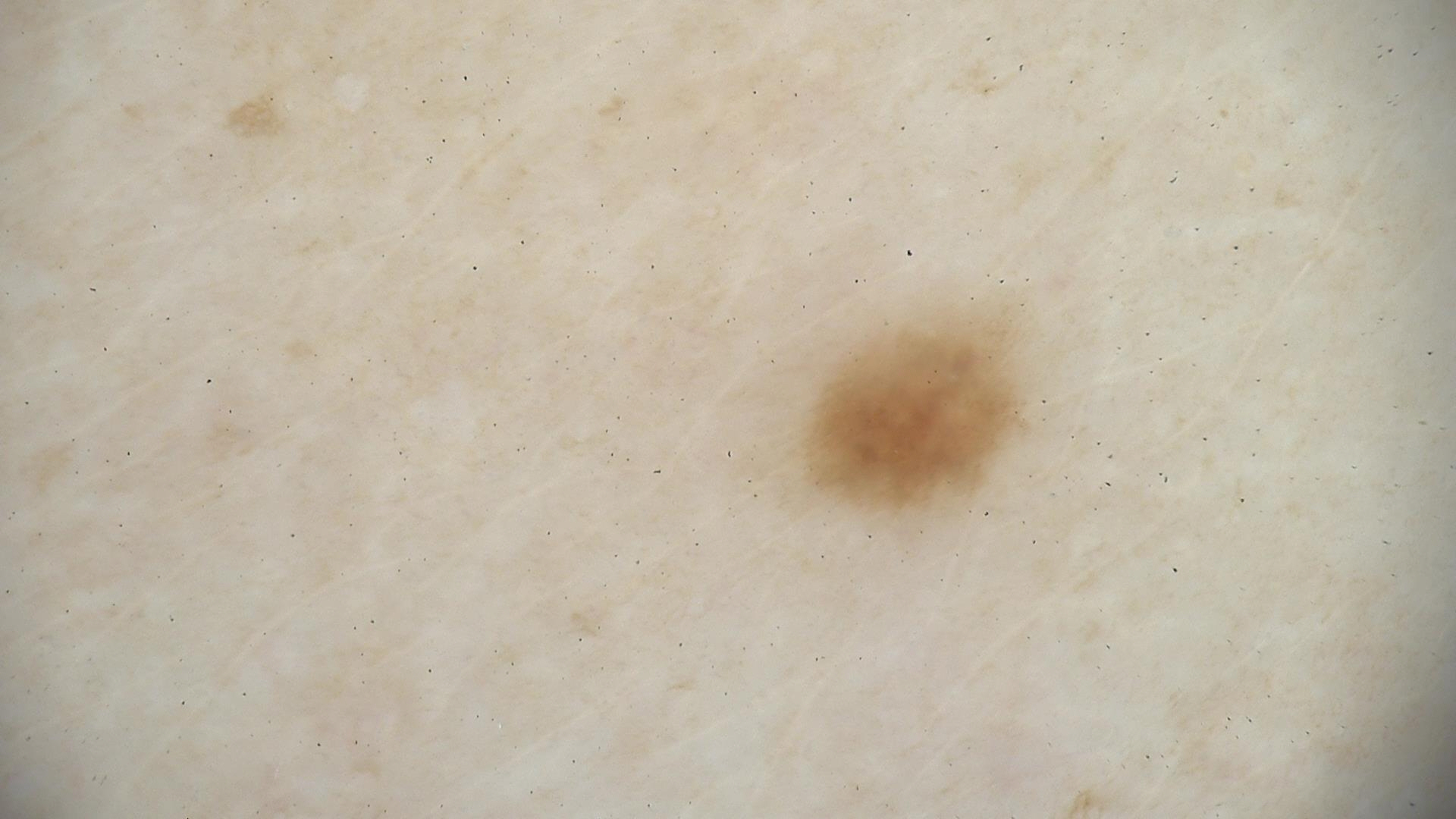assessment: junctional nevus (expert consensus).